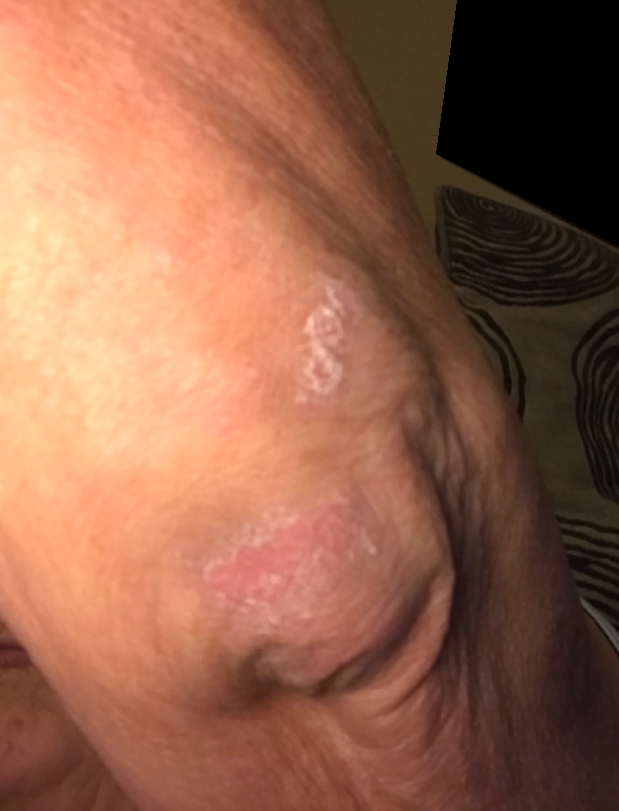The patient is 60–69, female.
Associated systemic symptoms include fatigue.
The patient indicates the lesion is raised or bumpy and rough or flaky.
The photo was captured at an angle.
The lesion is associated with itching, enlargement and bothersome appearance.
The patient considered this a rash.
On remote dermatologist review: the impression on review was Psoriasis.